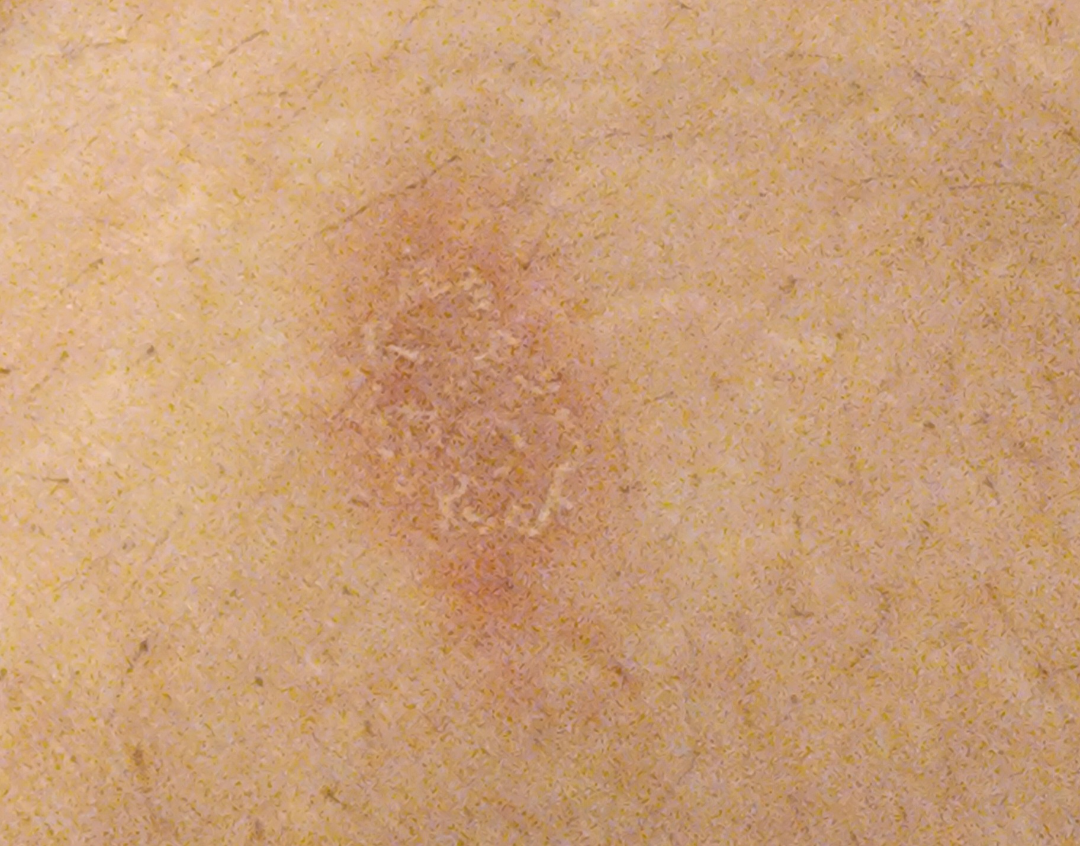assessment: ungradable on photographic review; framing: close-up.